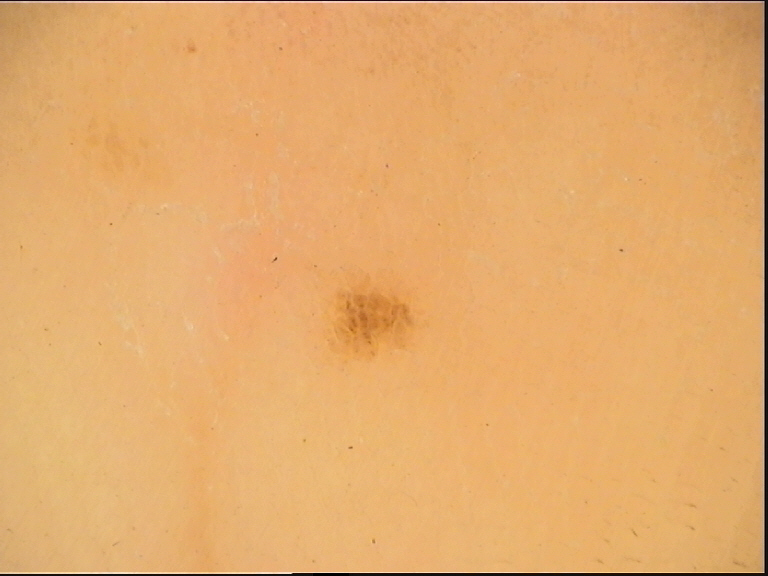The diagnostic label was a banal lesion — an acral junctional nevus.